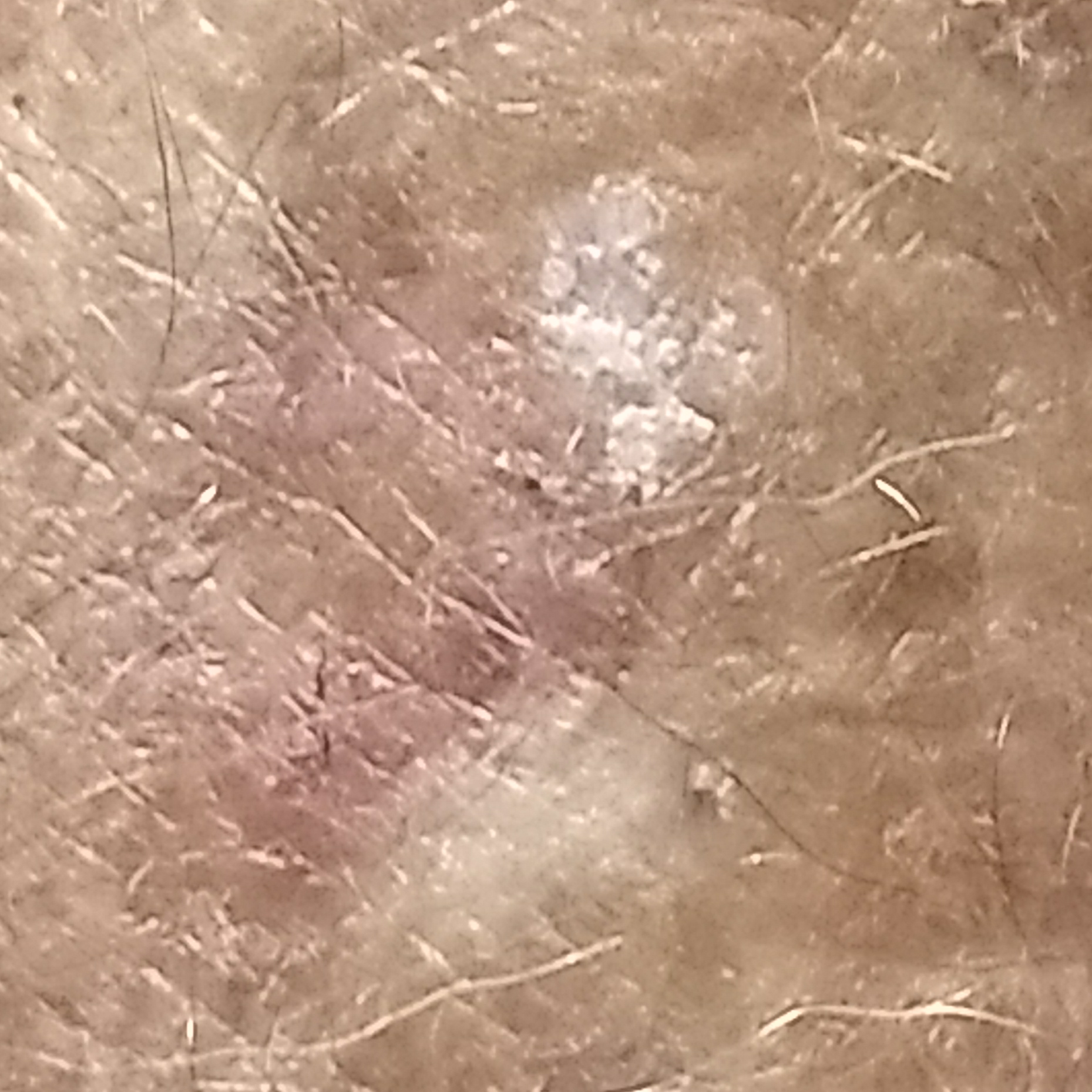Conclusion:
The diagnostic impression was an actinic keratosis.